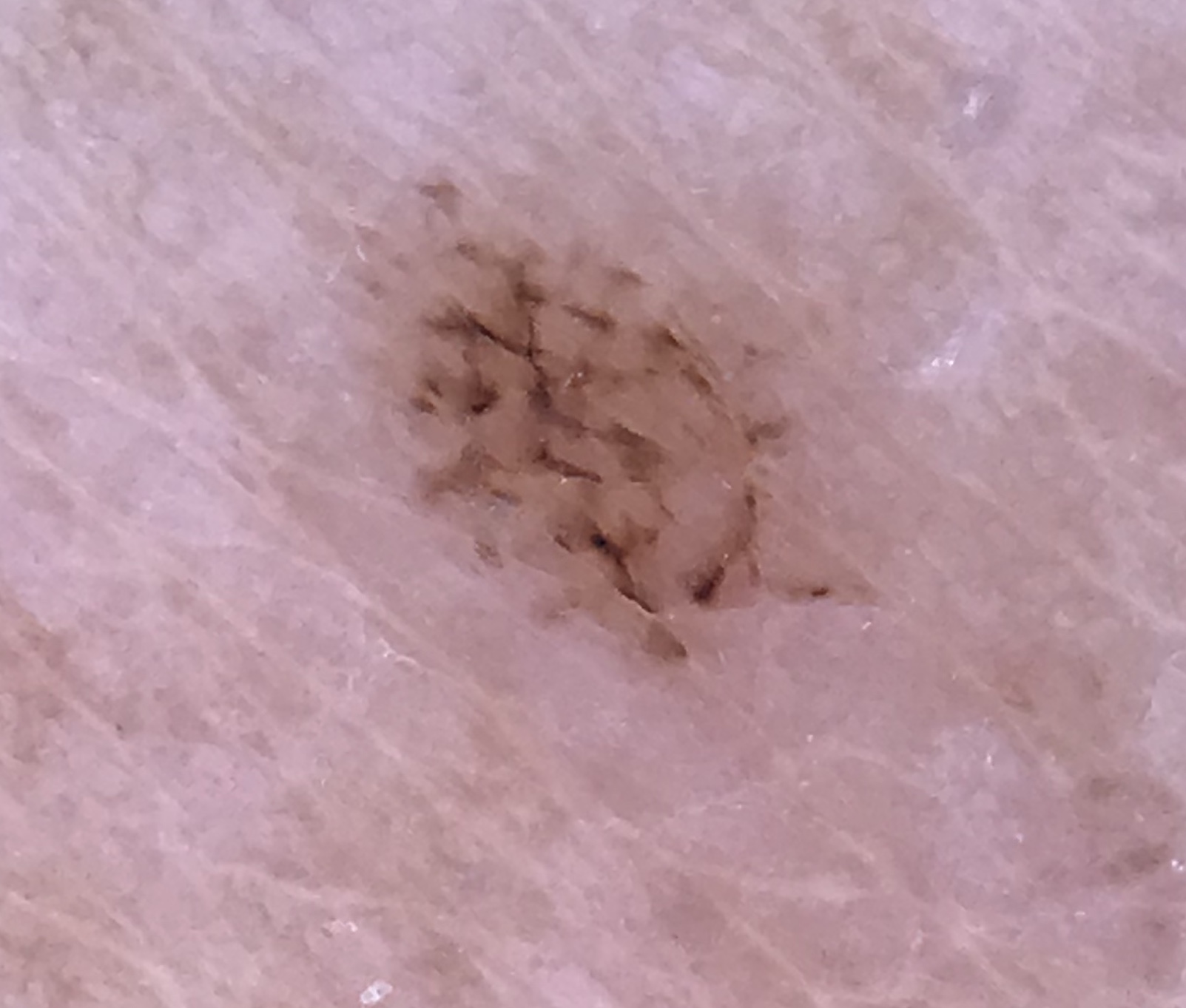diagnosis: acral dysplastic junctional nevus (expert consensus).